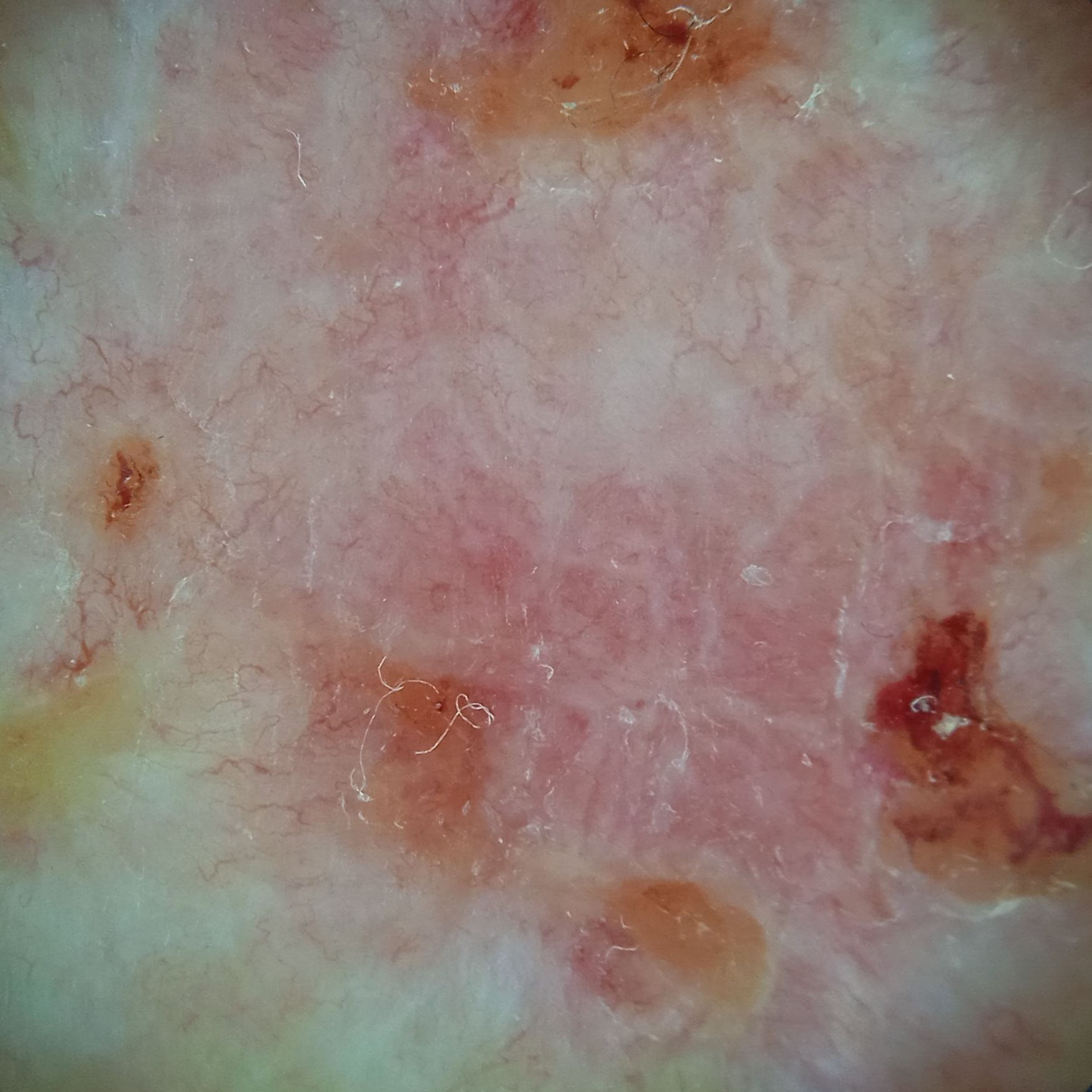Dermoscopy of a skin lesion. The patient describes having few moles overall. By self-report, a family history of skin cancer and a personal history of cancer. A male patient age 81. Referred for assessment of suspected basal cell carcinoma. The patient says their skin reddens with sun exposure. The lesion involves the back. The lesion measures approximately 12.6 mm. On biopsy, the diagnosis was a basal cell carcinoma, following excision, with a measured tumor thickness of 3 mm.